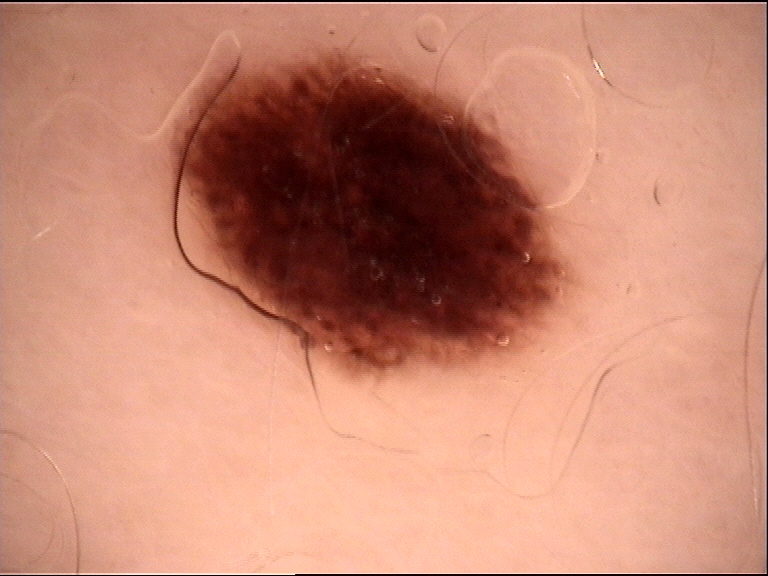The diagnostic label was a benign lesion — a dysplastic junctional nevus.